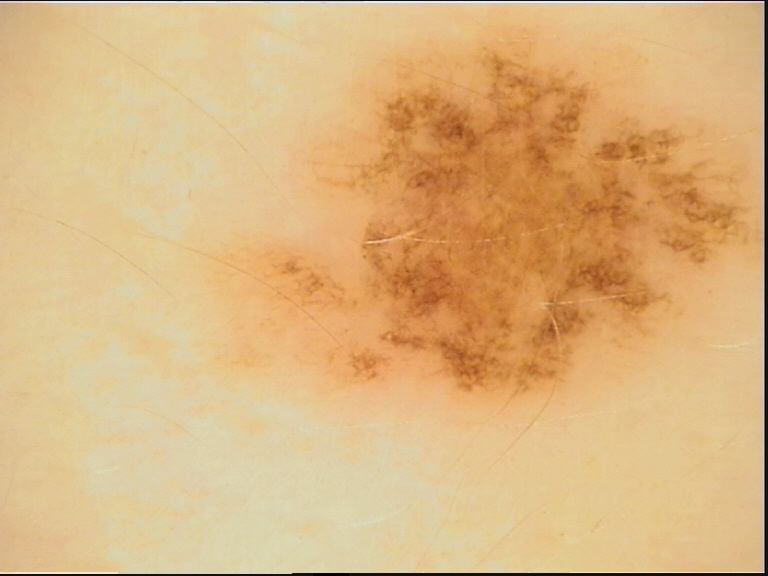image type: dermatoscopy; diagnosis: dysplastic junctional nevus (expert consensus).